The photograph is a close-up of the affected area · the arm is involved.
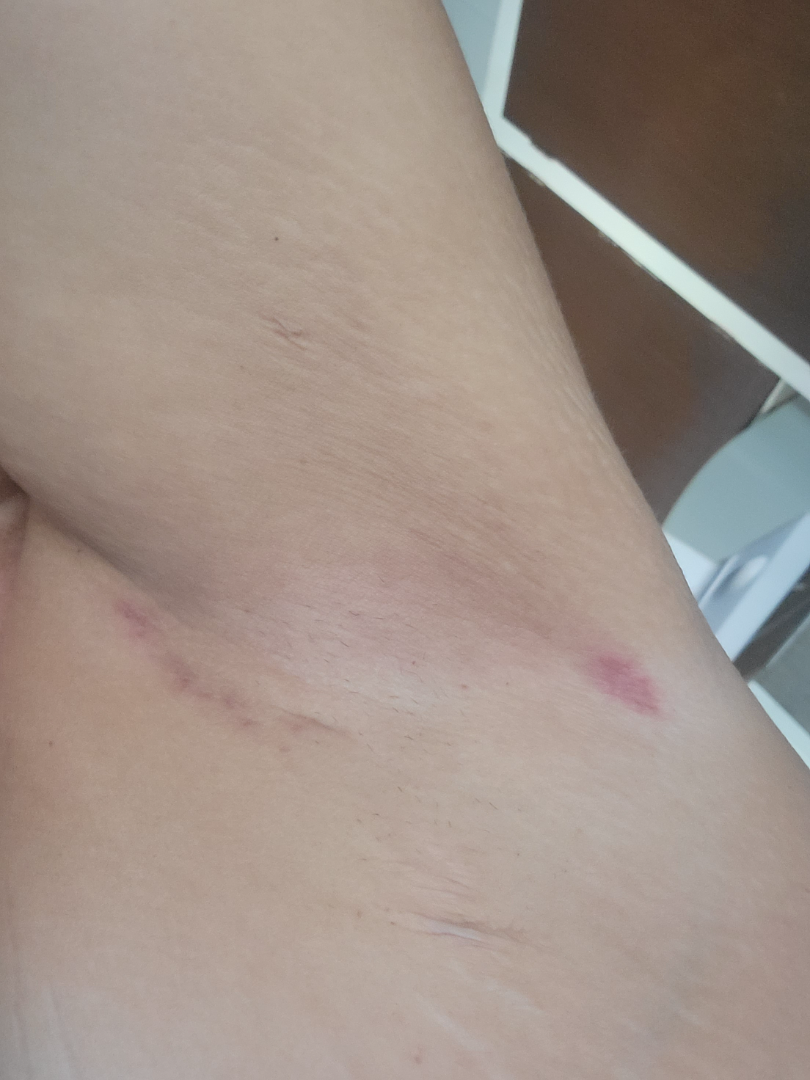{"symptoms": ["pain", "burning"], "texture": "flat", "systemic_symptoms": "none reported", "patient_category": "a rash", "duration": "about one day", "differential": {"leading": ["Hidradenitis"], "considered": ["Abscess"]}}